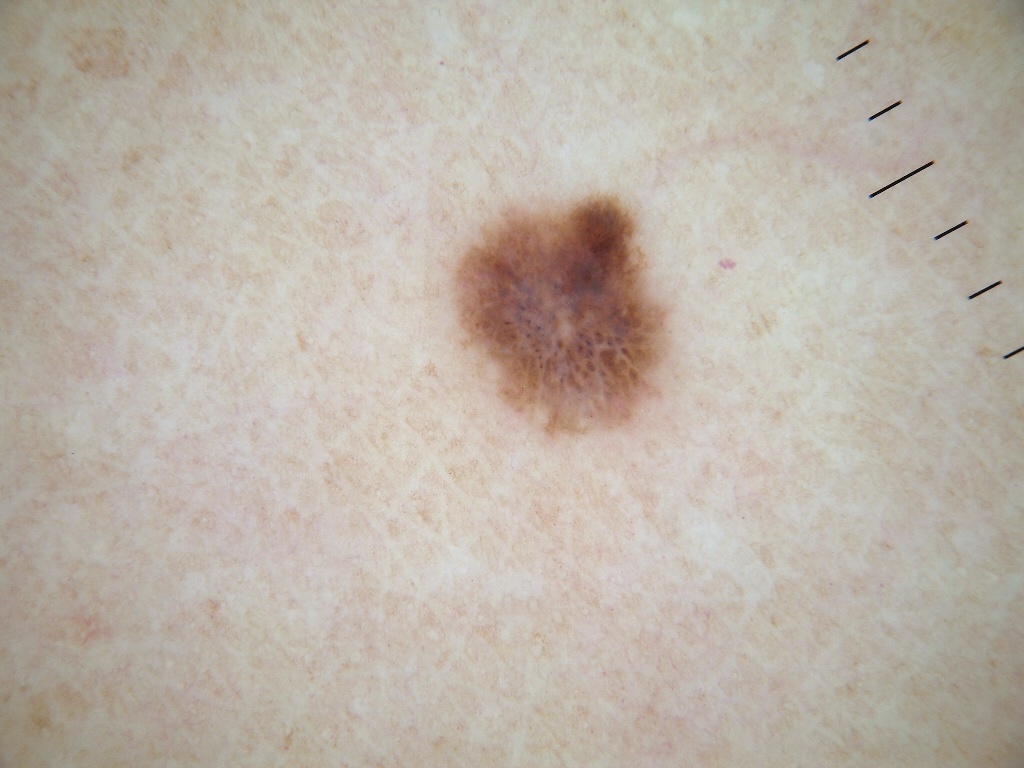image — dermatoscopic image of a skin lesion; patient — female, approximately 30 years of age; lesion location — x1=455, y1=195, x2=665, y2=432; dermoscopic findings — globules and negative network; extent — ~5% of the field; impression — a melanocytic nevus, a benign lesion.